Located on the leg, a close-up photograph.
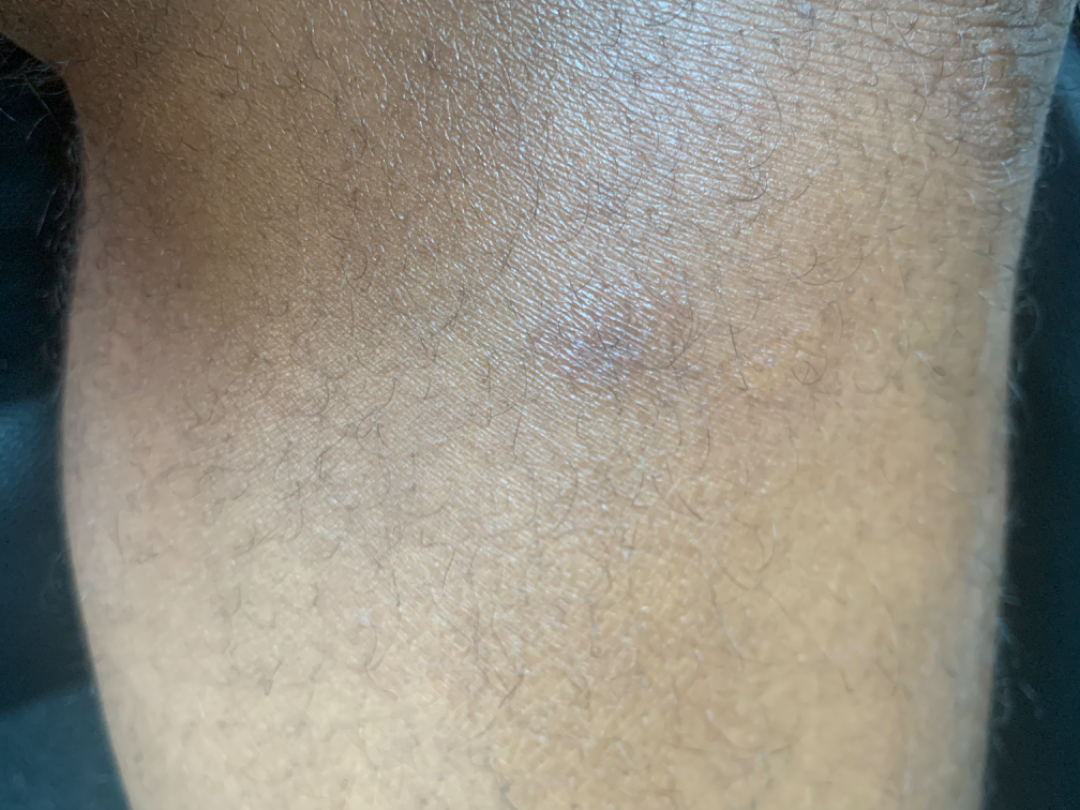Q: What was the assessment?
A: not assessable